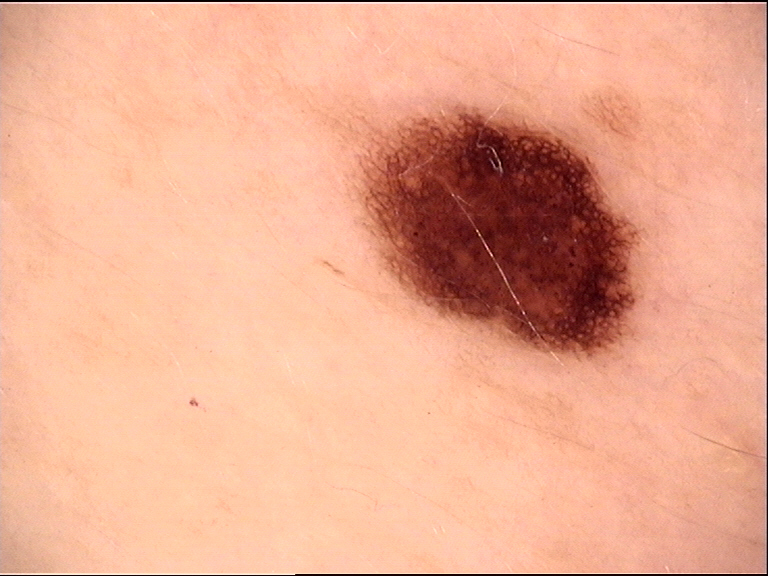imaging: dermoscopy
class: dysplastic junctional nevus (expert consensus)